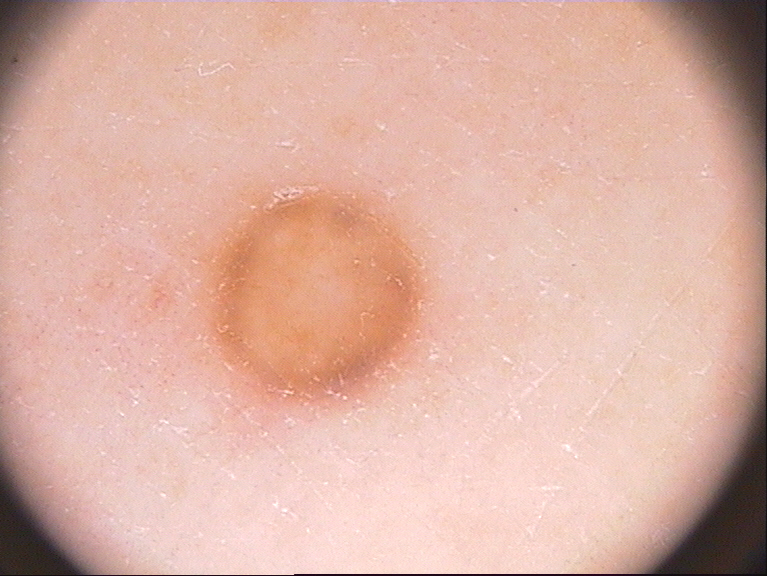Findings:
* image type: dermatoscopic image of a skin lesion
* lesion location: [209, 194, 420, 395]
* dermoscopic features not present: negative network, pigment network, milia-like cysts, streaks, and globules
* diagnostic label: a melanocytic nevus, a benign skin lesion